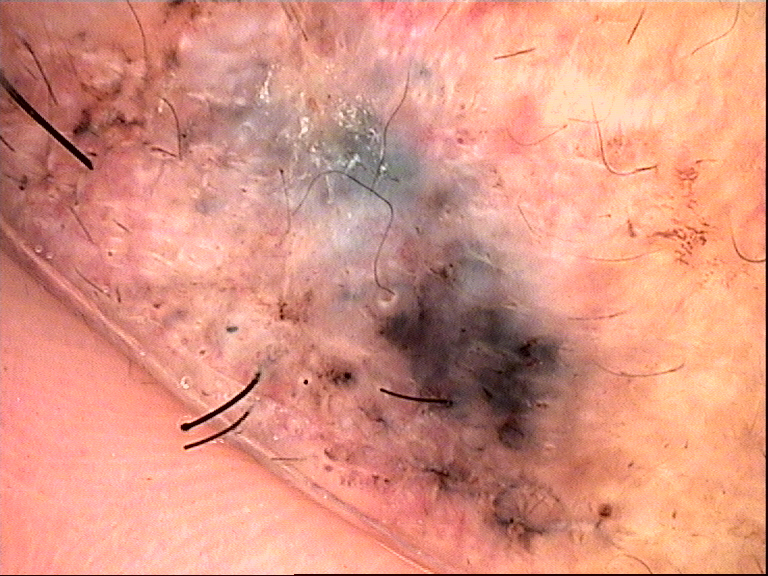| key | value |
|---|---|
| image type | dermoscopy |
| subtype | keratinocytic |
| diagnosis | basal cell carcinoma (biopsy-proven) |